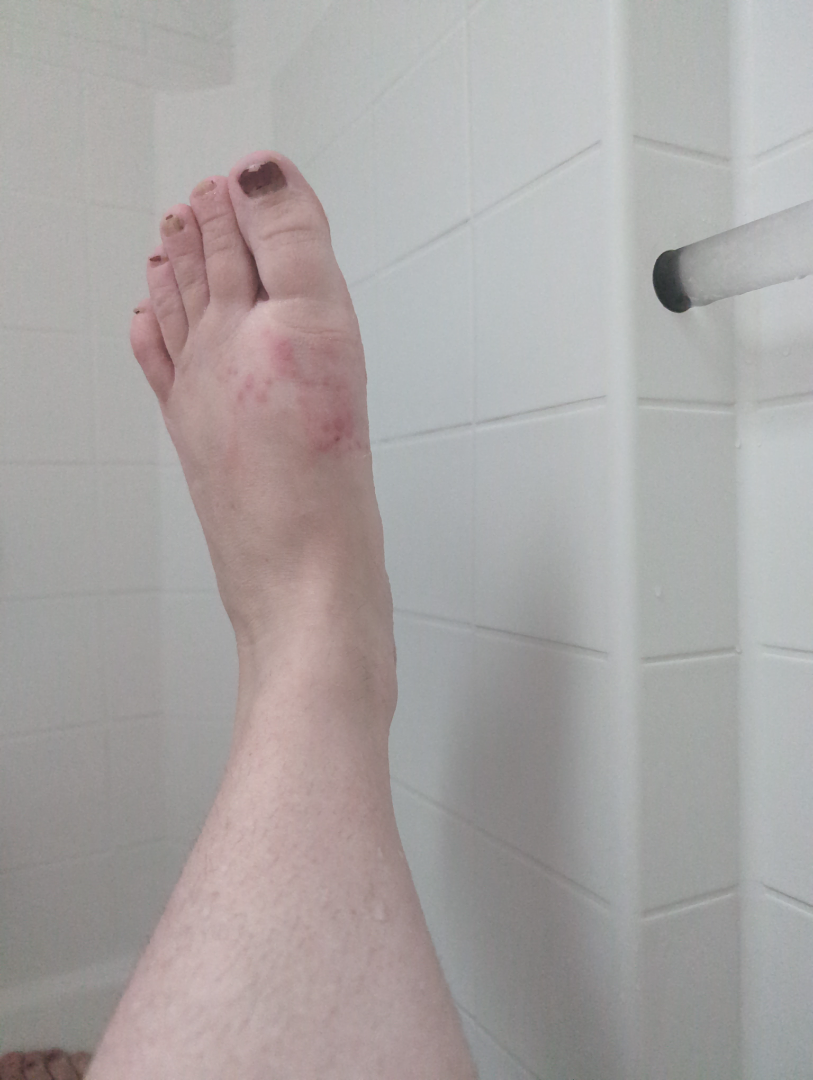texture=rough or flaky and raised or bumpy | body site=top or side of the foot and sole of the foot | patient describes the issue as=a rash | onset=three to twelve months | subject=female | framing=at a distance | skin tone=Fitzpatrick phototype II; lay graders estimated MST 1–2 | diagnostic considerations=consistent with Eczema.